Dermoscopy of a skin lesion.
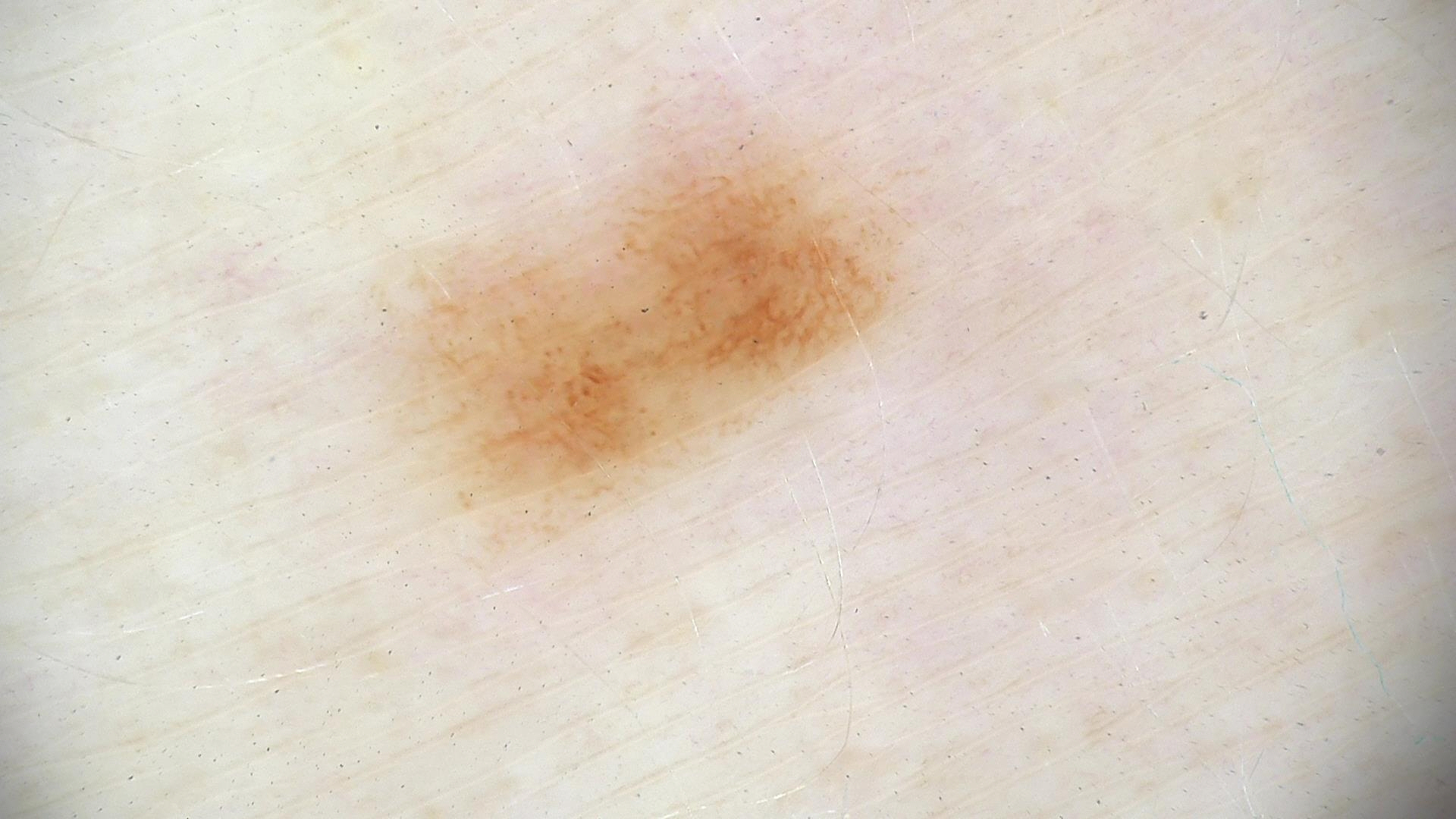Conclusion: Labeled as a benign lesion — a dysplastic junctional nevus.